The photograph is a close-up of the affected area. No relevant systemic symptoms. Symptoms reported: bothersome appearance. The lesion is described as flat. Present for less than one week. The patient considered this a rash. The back of the hand, top or side of the foot, head or neck, front of the torso, back of the torso, arm, palm, leg and sole of the foot are involved: 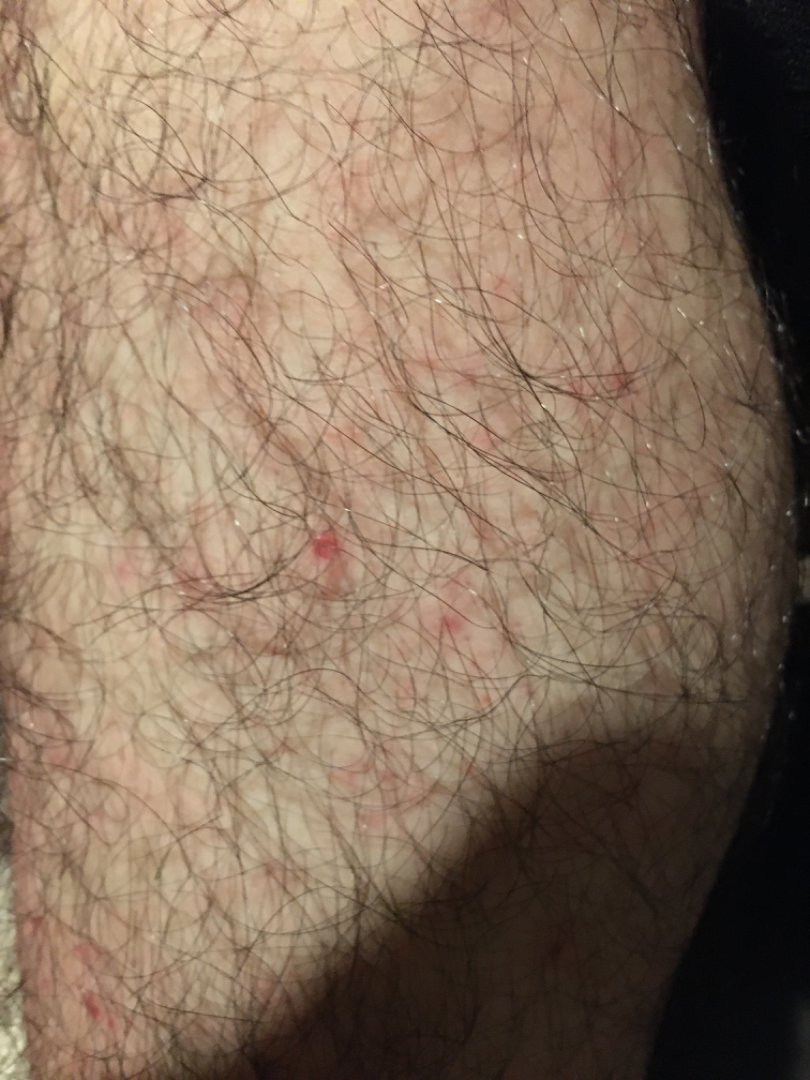Folliculitis, Eczema and Allergic Contact Dermatitis were considered with similar weight.